A skin lesion imaged with a dermatoscope: 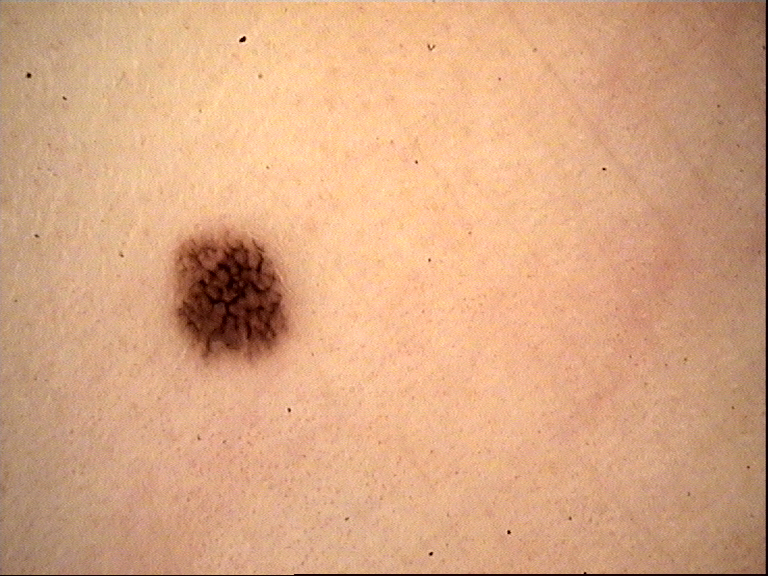diagnosis — dysplastic junctional nevus (expert consensus).